An image taken at an angle: 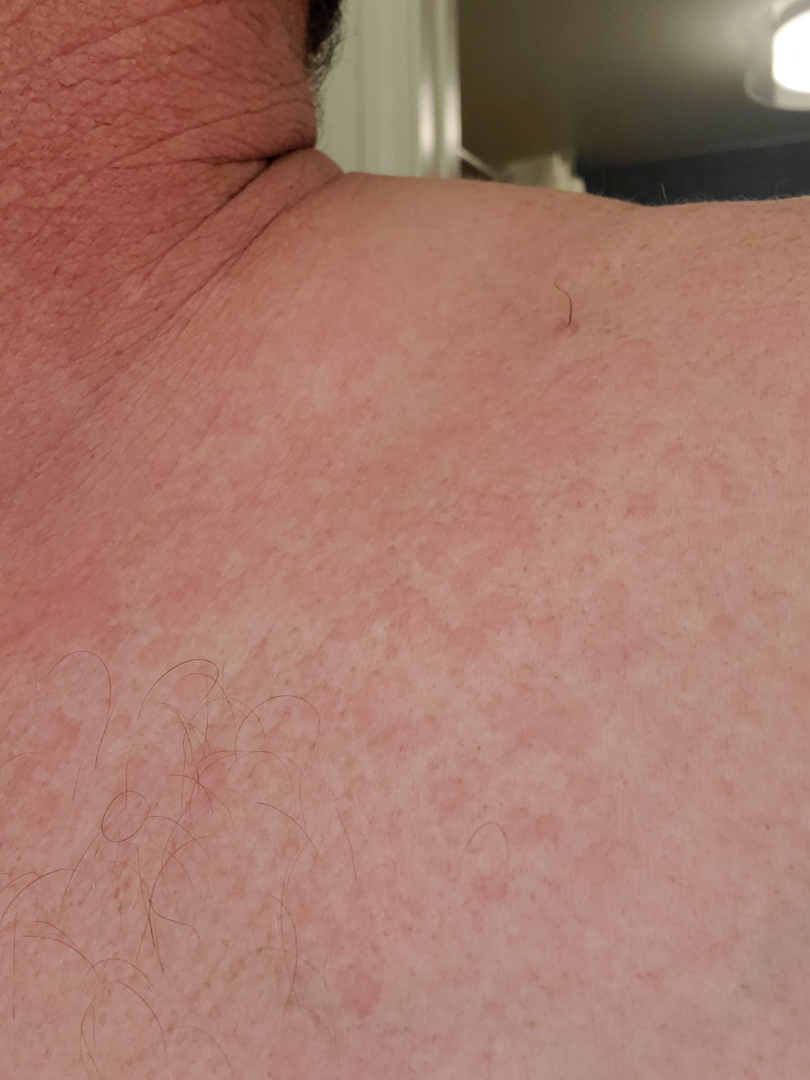differential diagnosis=the reviewer's impression was Tinea Versicolor.